A dermoscopy image of a single skin lesion.
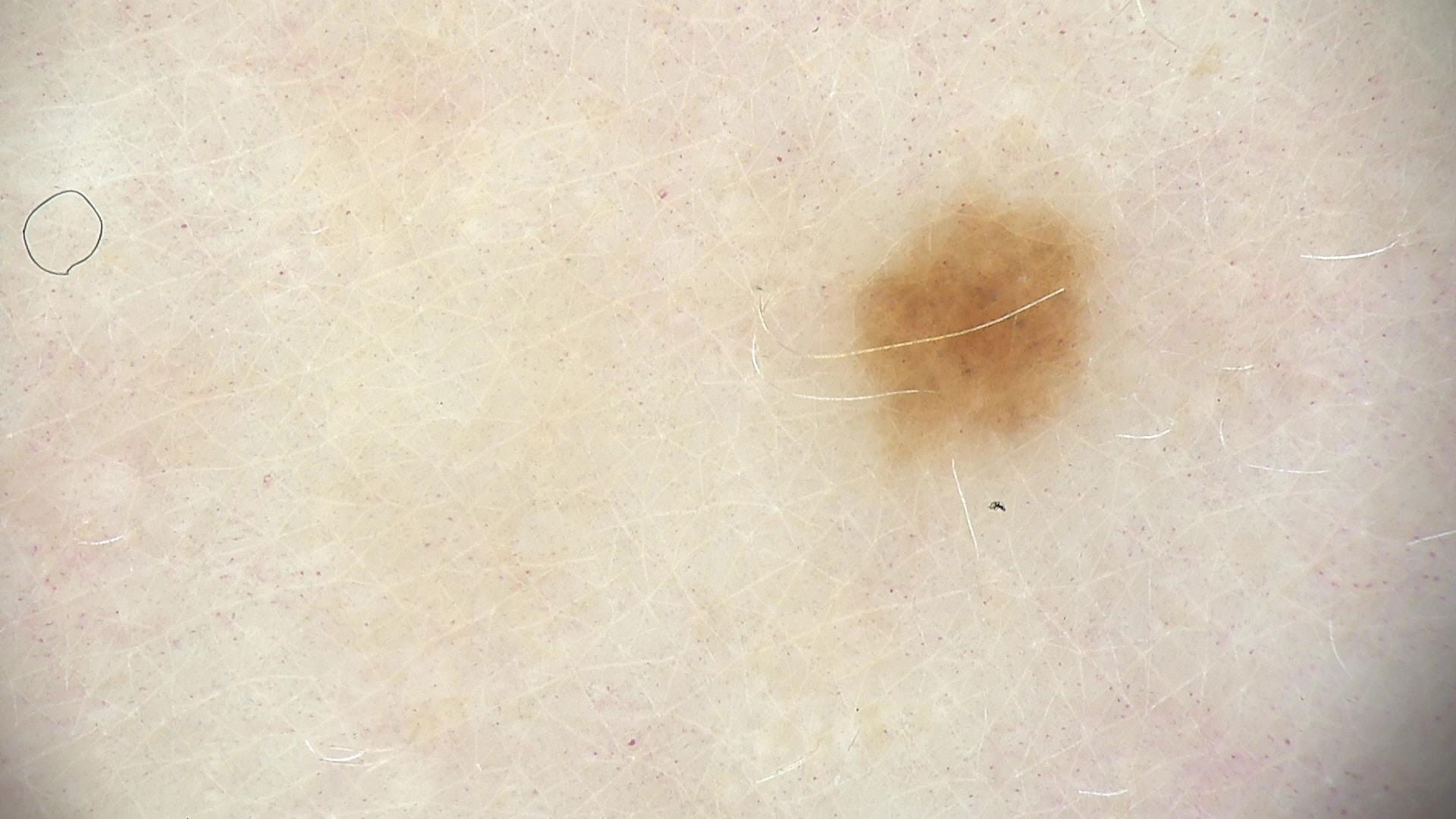Impression:
The diagnostic label was a banal lesion — a junctional nevus.